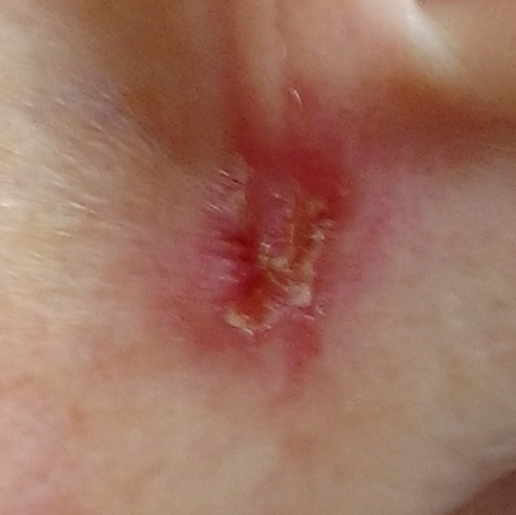{"image": "clinical photograph", "lesion_location": "an ear", "symptoms": {"present": ["pain", "bleeding", "itching"], "absent": ["elevation"]}, "diagnosis": {"name": "basal cell carcinoma", "code": "BCC", "malignancy": "malignant", "confirmation": "histopathology"}}